The lesion involves the arm; the patient described the issue as skin that appeared healthy to them; this image was taken at an angle; the patient is a male aged 18–29 — 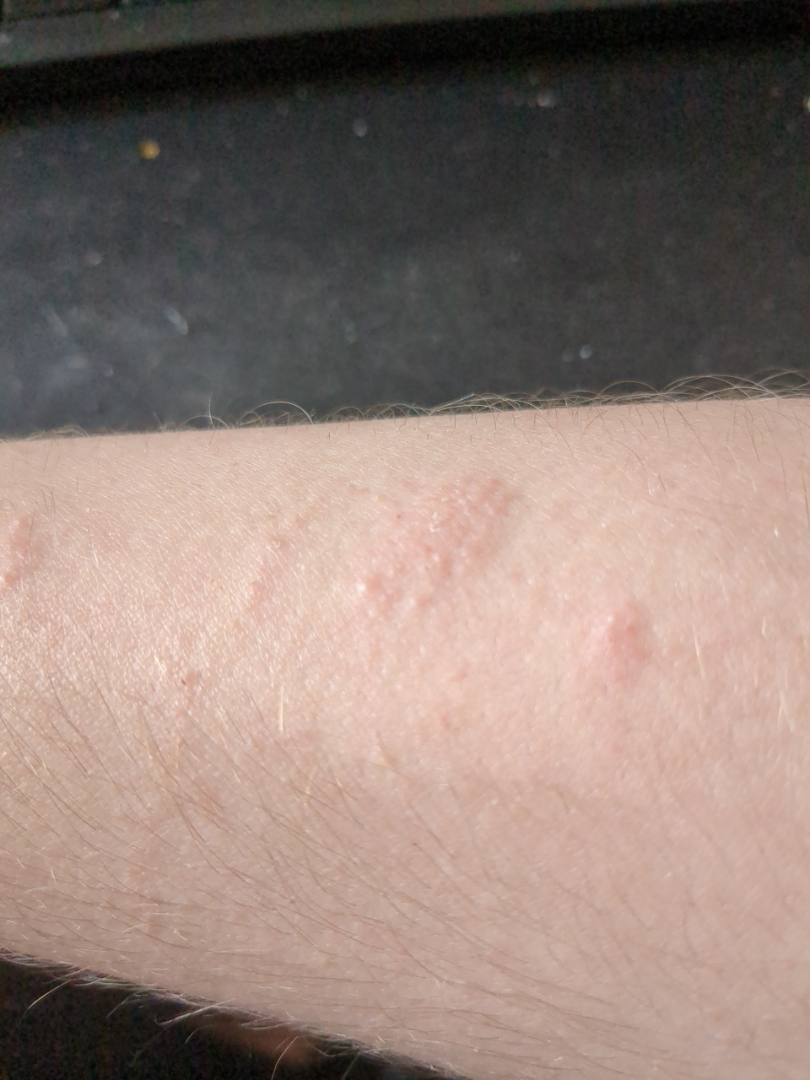Consistent with Allergic Contact Dermatitis.